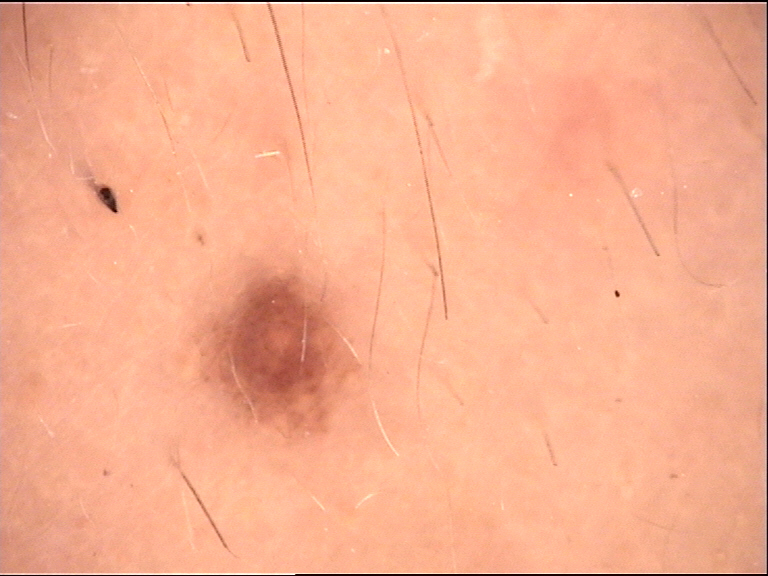Labeled as a banal lesion — a dermal nevus.